A dermoscopy image of a single skin lesion.
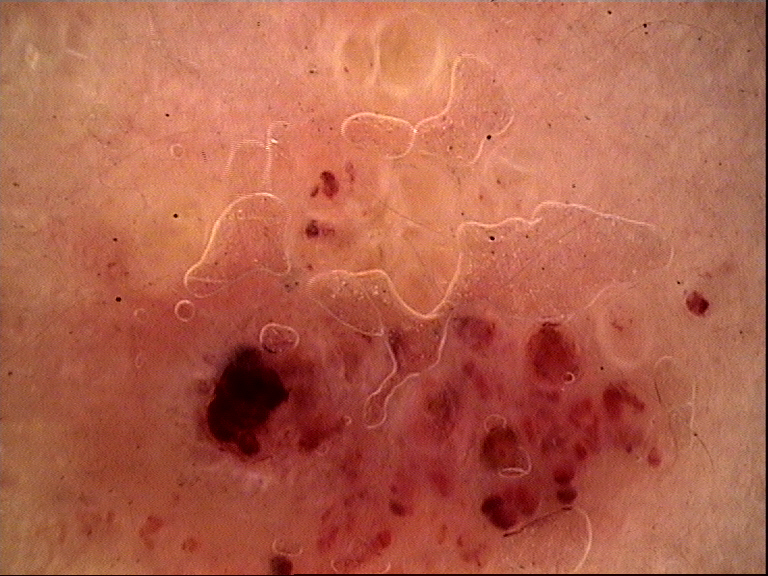The diagnostic label was a vascular, benign lesion — a lymphangioma.